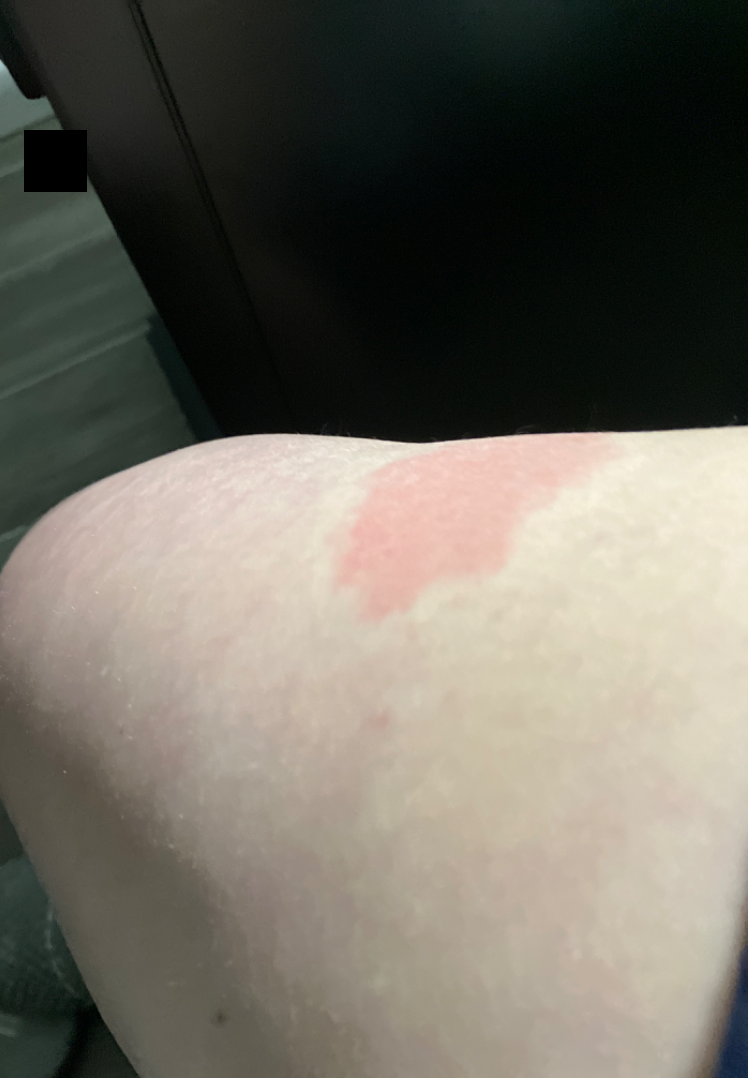Case summary:
– assessment — unable to determine
– shot type — at an angle
– anatomic site — leg